A male subject roughly 70 years of age. A skin lesion imaged with contact-polarized dermoscopy. FST II — 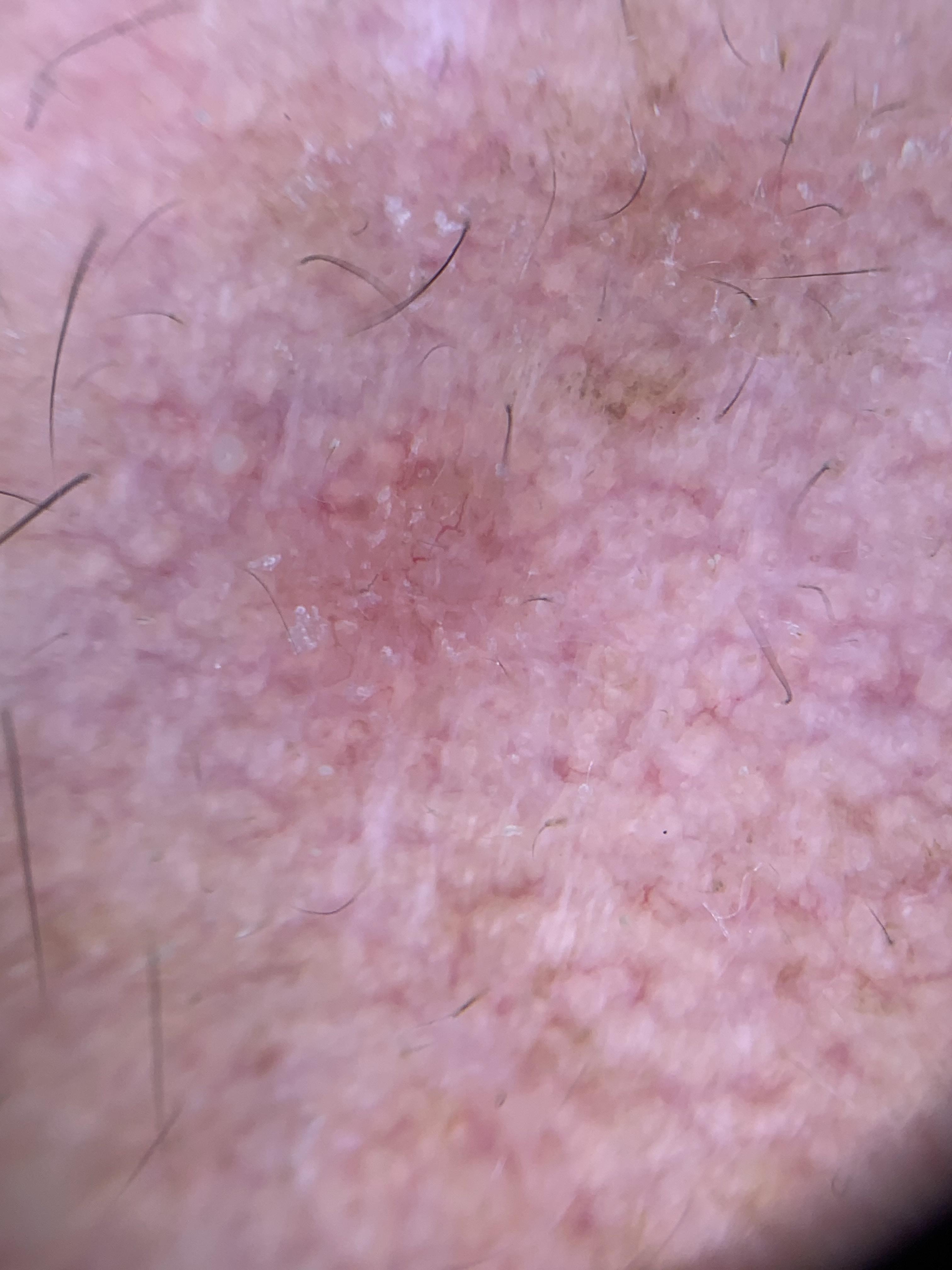{
  "lesion_location": {
    "region": "the head or neck"
  },
  "diagnosis": {
    "name": "Basal cell carcinoma",
    "malignancy": "malignant",
    "confirmation": "histopathology",
    "lineage": "adnexal"
  }
}